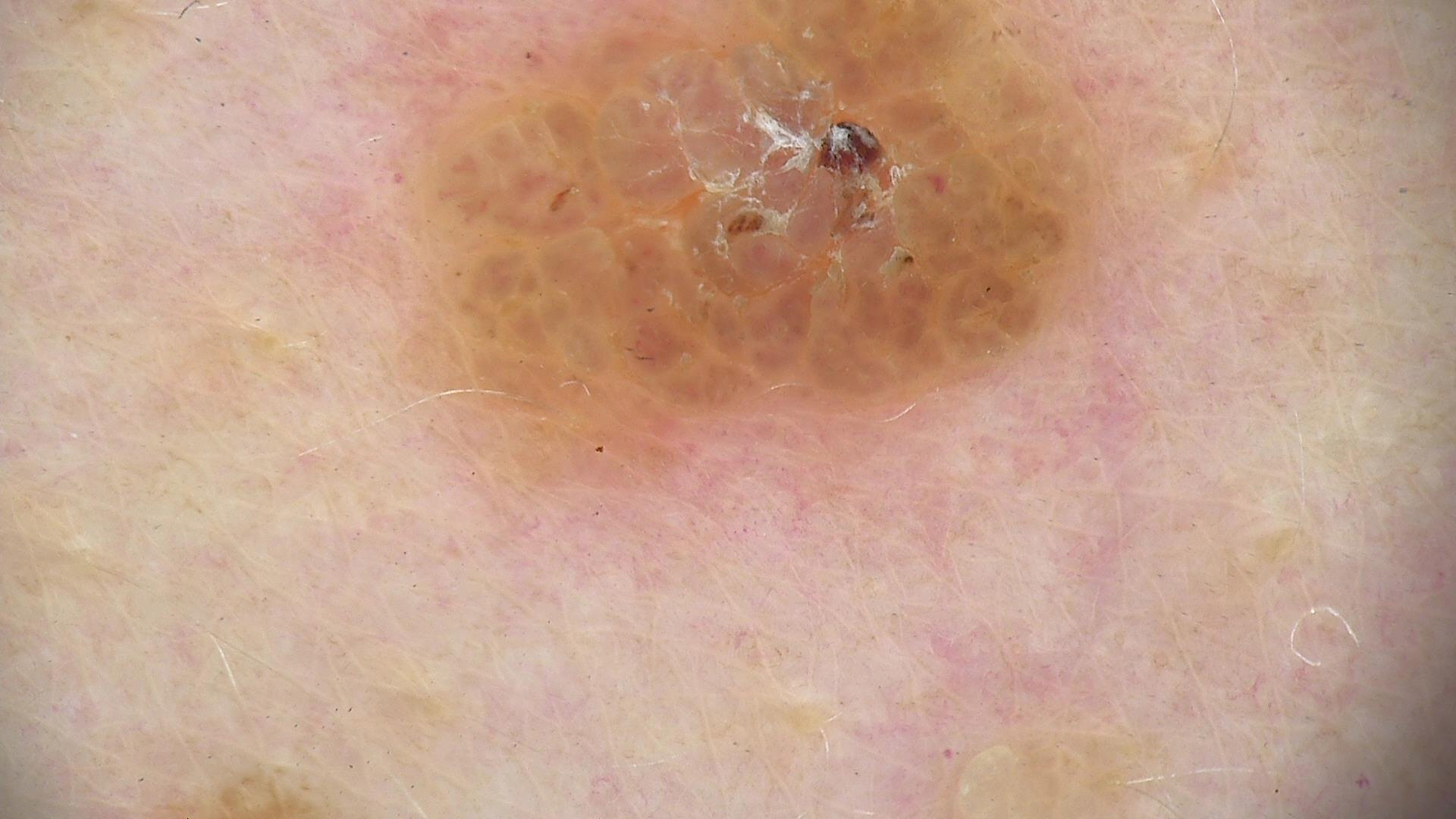assessment = seborrheic keratosis (expert consensus)